Dermoscopy of a skin lesion.
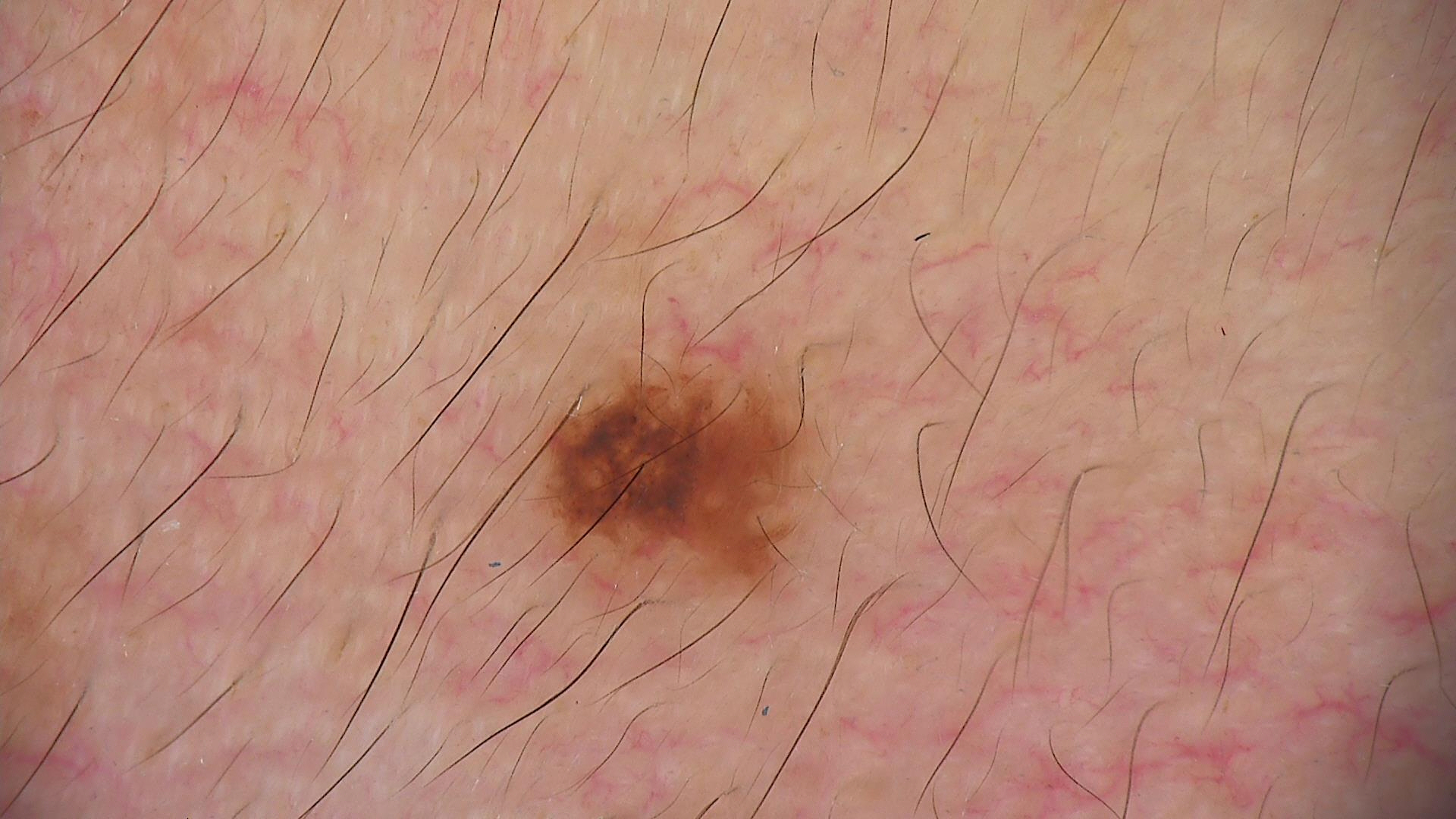class=Miescher nevus (expert consensus).